A dermatoscopic image of a skin lesion.
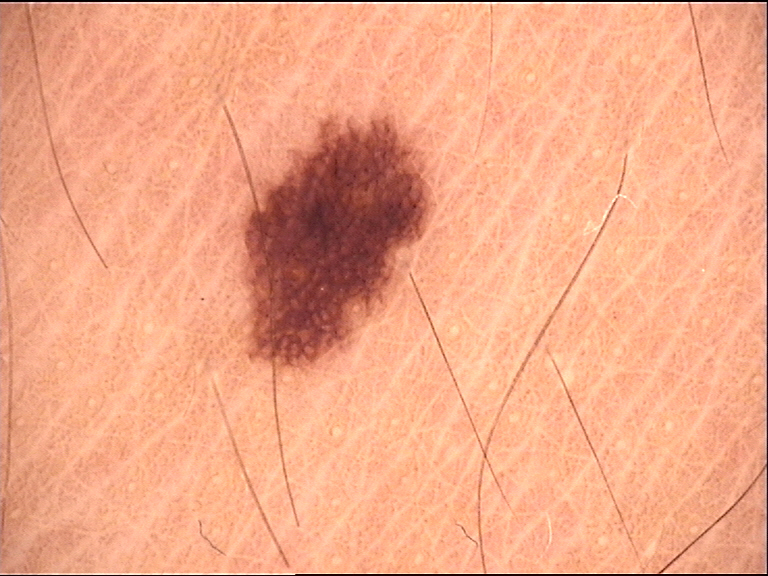Findings:
* diagnosis · junctional nevus (expert consensus)